A skin lesion imaged with a dermatoscope; collected as part of a research study, without a referral diagnosis; a male subject 62 years of age — 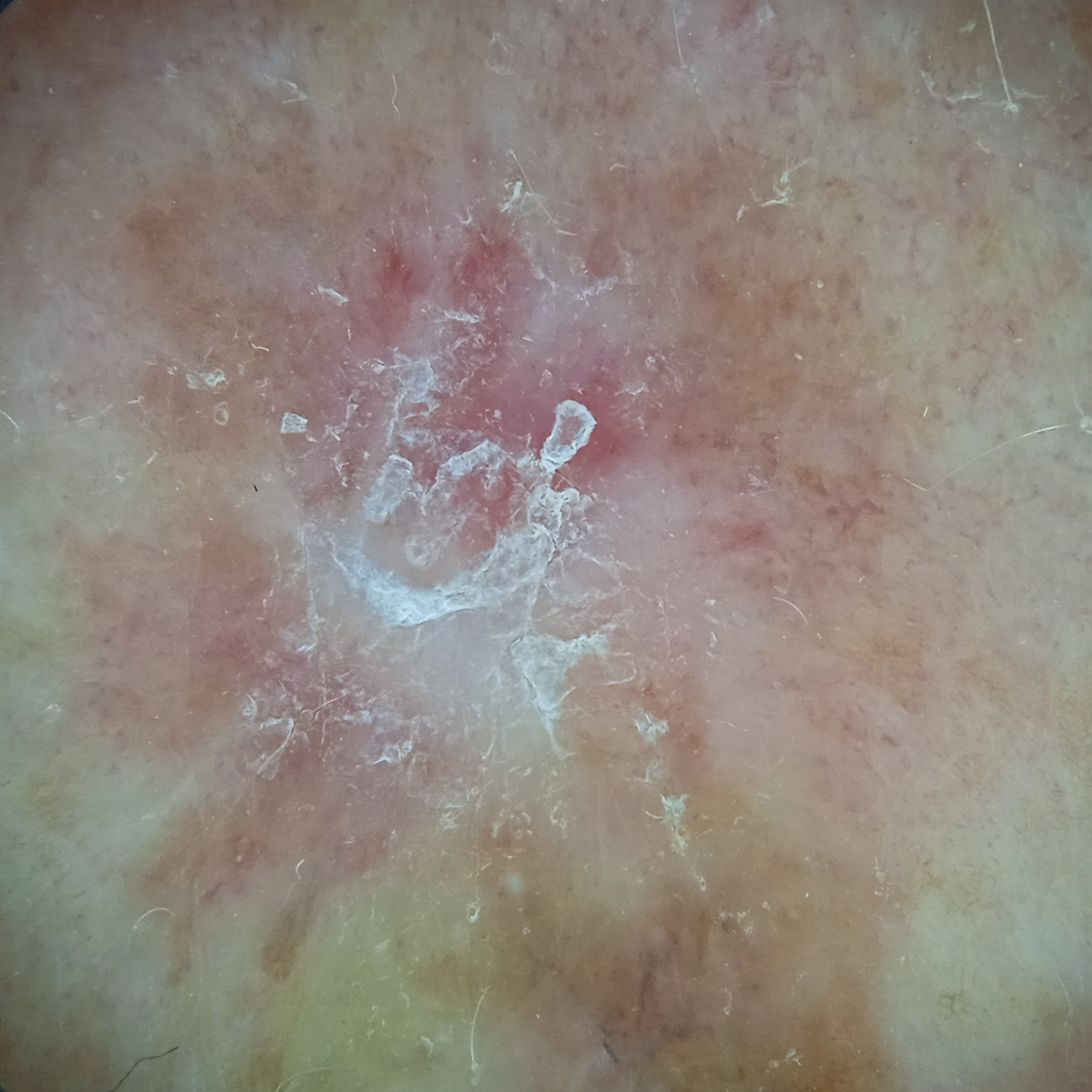Case:
- site · the back
- size · 13.8 mm
- assessment · squamous cell carcinoma (dermatologist consensus)